Collected as part of a research study, without a referral diagnosis; dermoscopy of a skin lesion; the patient says their skin tans without first burning; by self-report, a personal history of skin cancer, a personal history of cancer, and no family history of skin cancer: 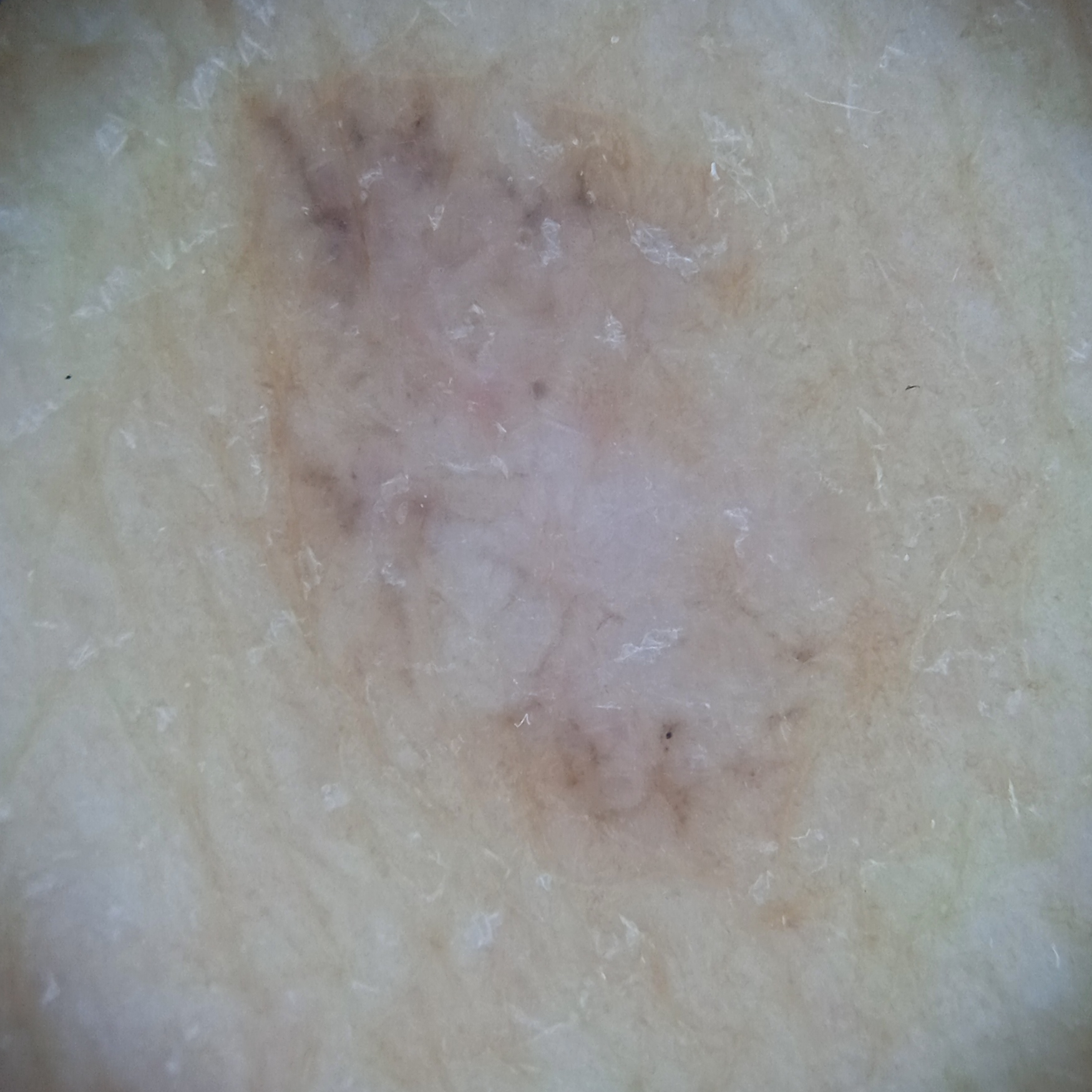Summary: The lesion is located on the back. The lesion measures approximately 10.4 mm. Conclusion: The lesion was assessed as a basal cell carcinoma.